A dermoscopic image of a skin lesion:
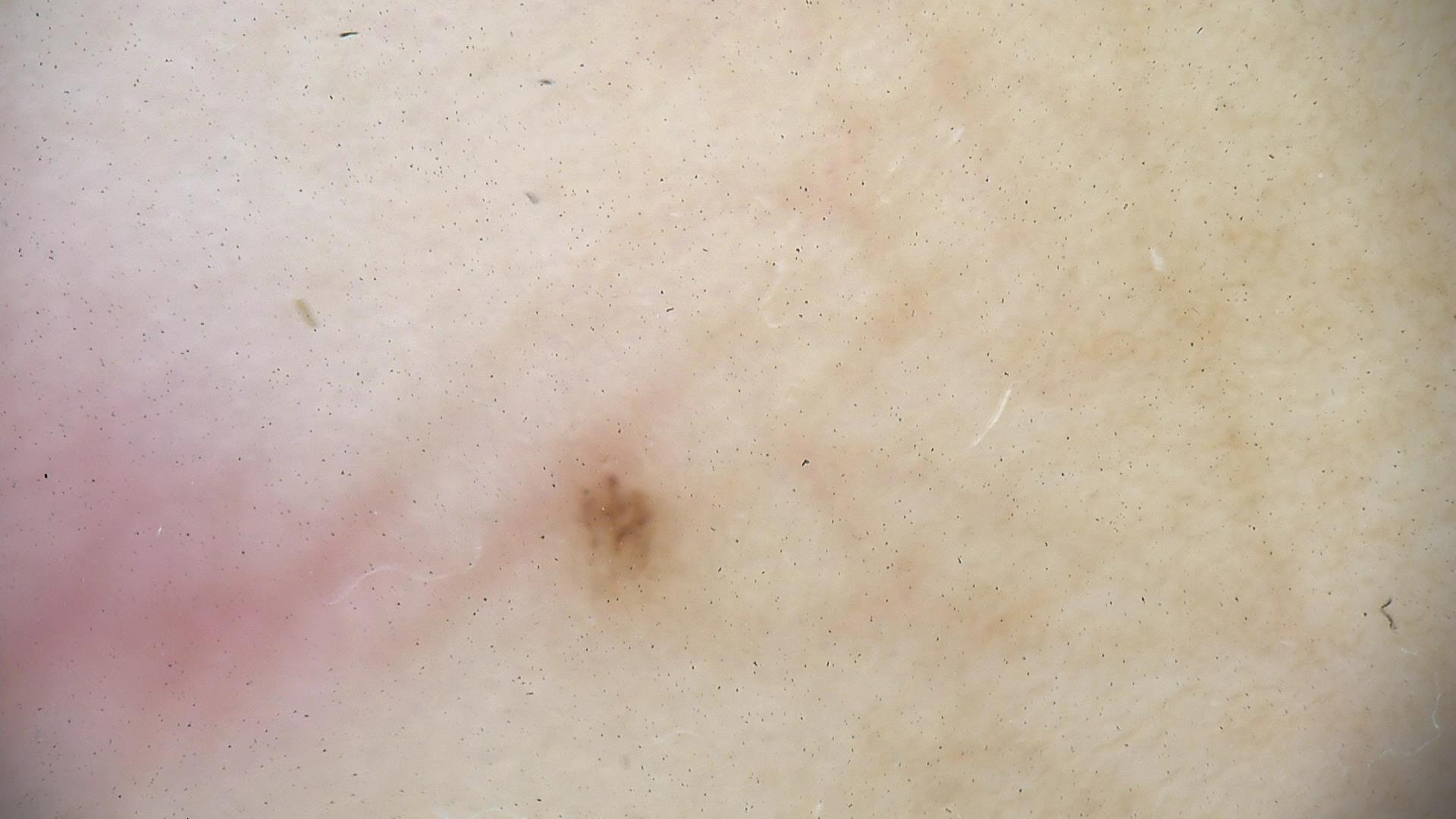Diagnosed as a benign lesion — an acral dysplastic junctional nevus.